The photograph is a close-up of the affected area: 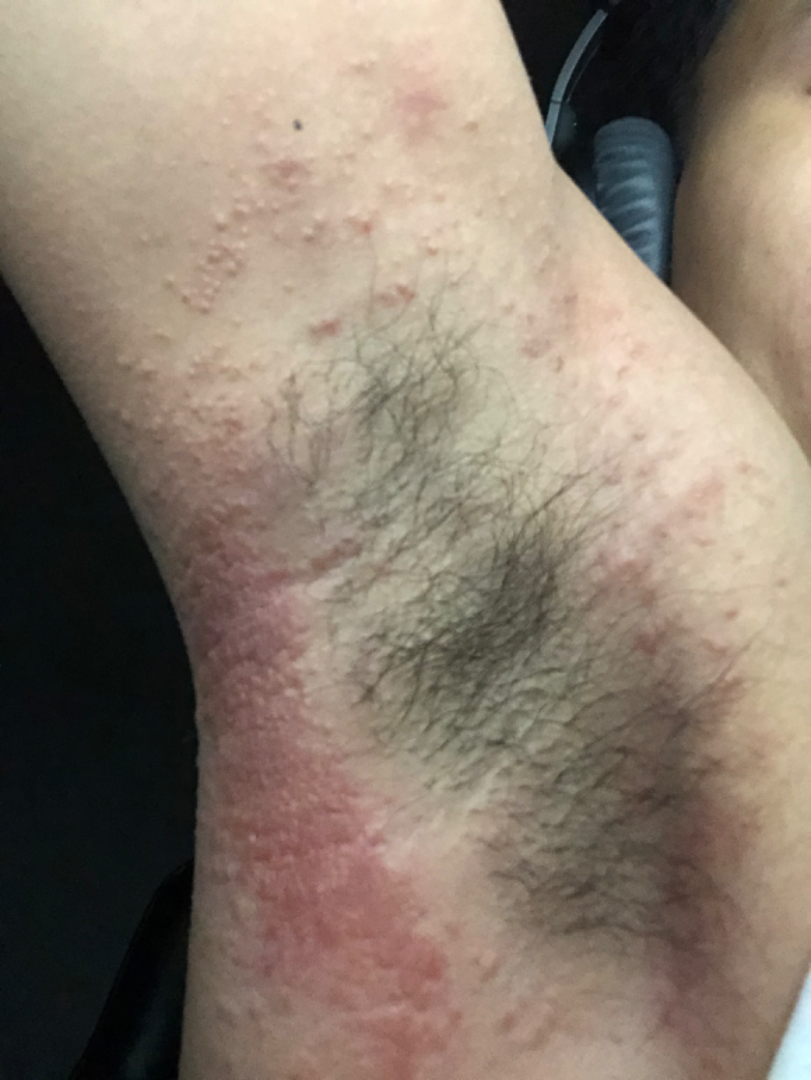Allergic Contact Dermatitis (0.50); Irritant Contact Dermatitis (0.50).